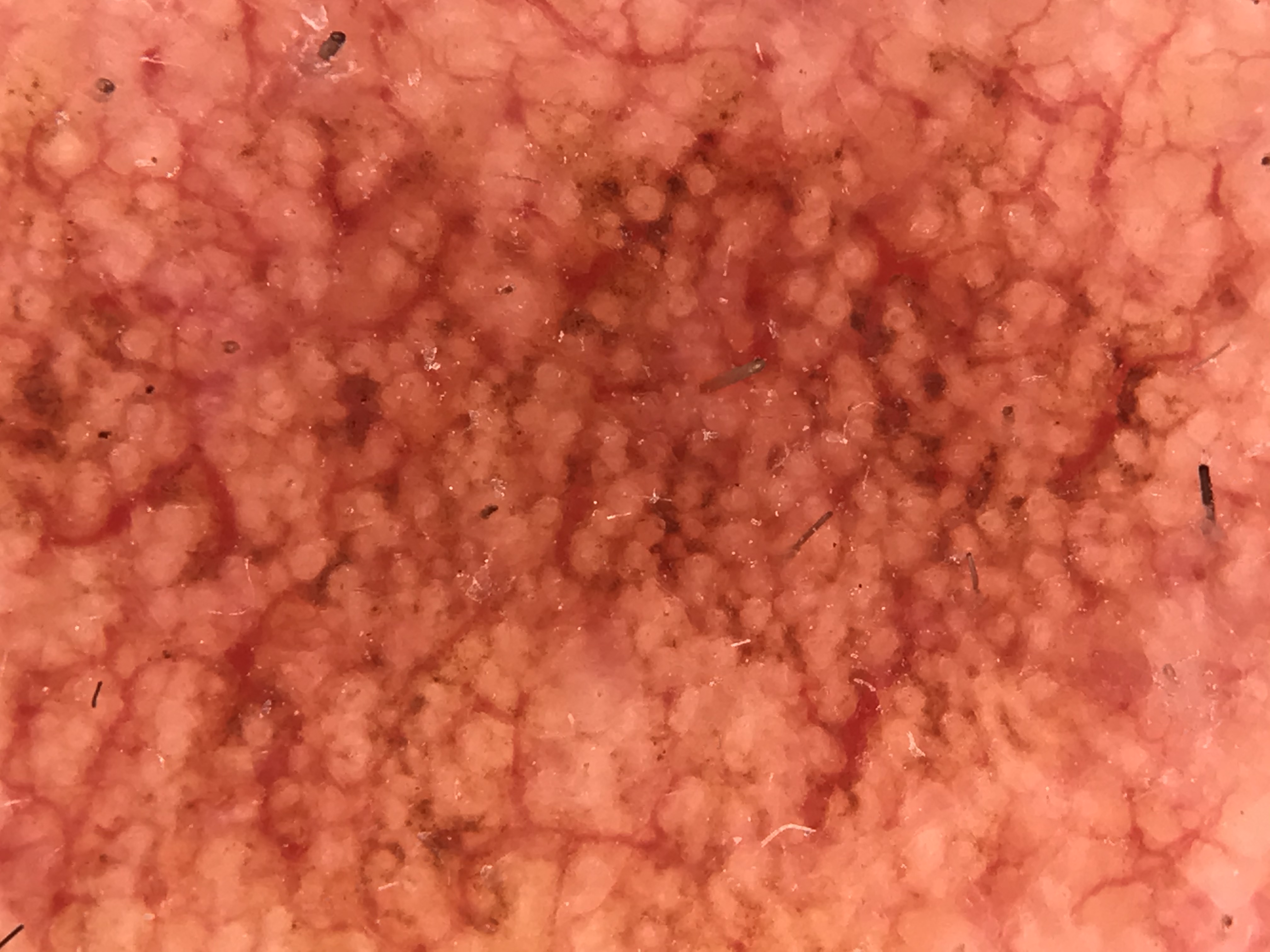The diagnostic label was an actinic keratosis.